This image was taken at an angle, the patient is a female aged 18–29, the affected area is the leg.
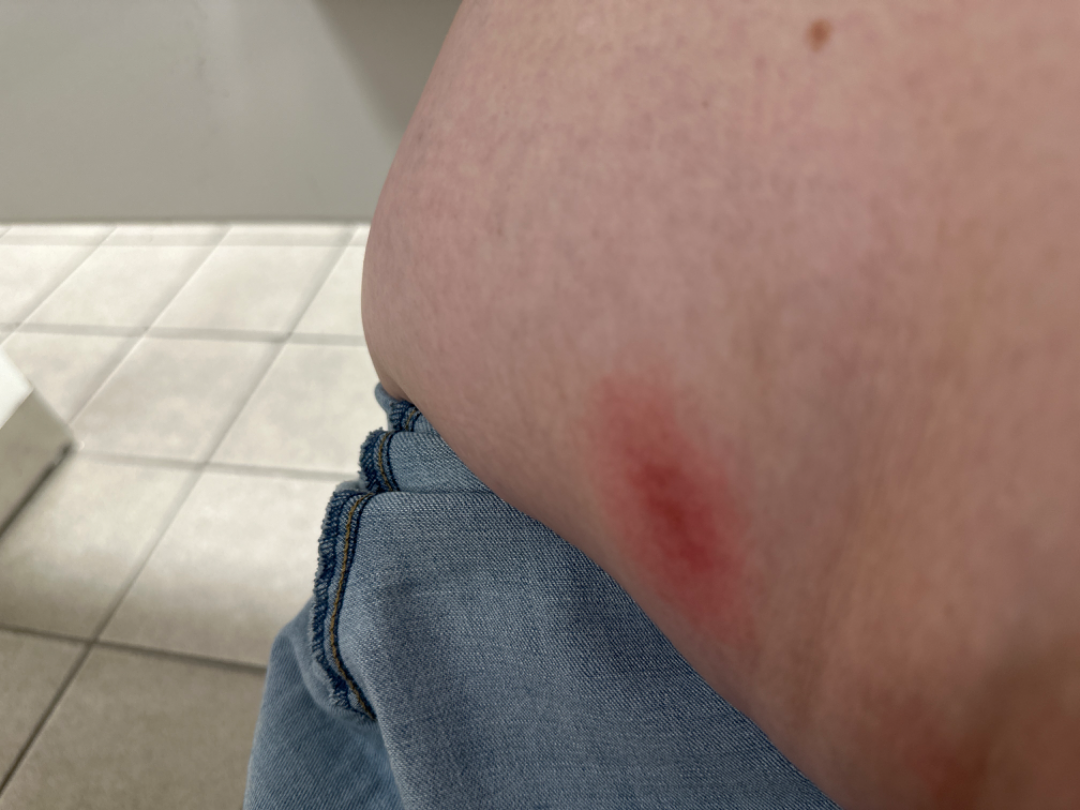Reported duration is about one day.
The patient described the issue as a rash.
Texture is reported as raised or bumpy.
Symptoms reported: burning, pain and itching.
One reviewing dermatologist: favoring Eczema; possibly Geographic tongue.